A female subject about 80 years old · Fitzpatrick phototype II · a dermoscopic photograph of a skin lesion — 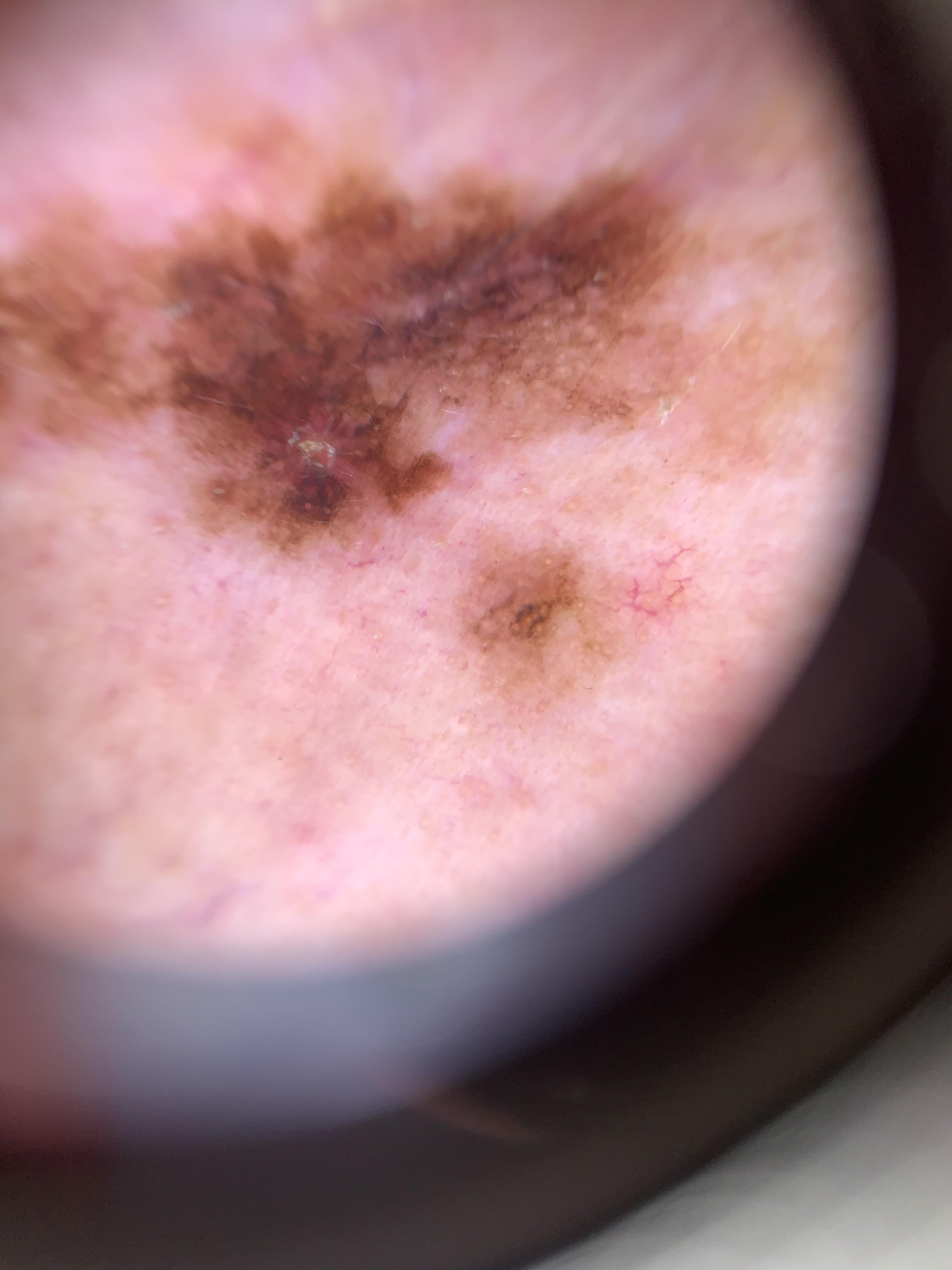{
  "lesion_location": {
    "region": "the head or neck"
  },
  "diagnosis": {
    "name": "Melanoma",
    "malignancy": "malignant",
    "confirmation": "histopathology"
  }
}